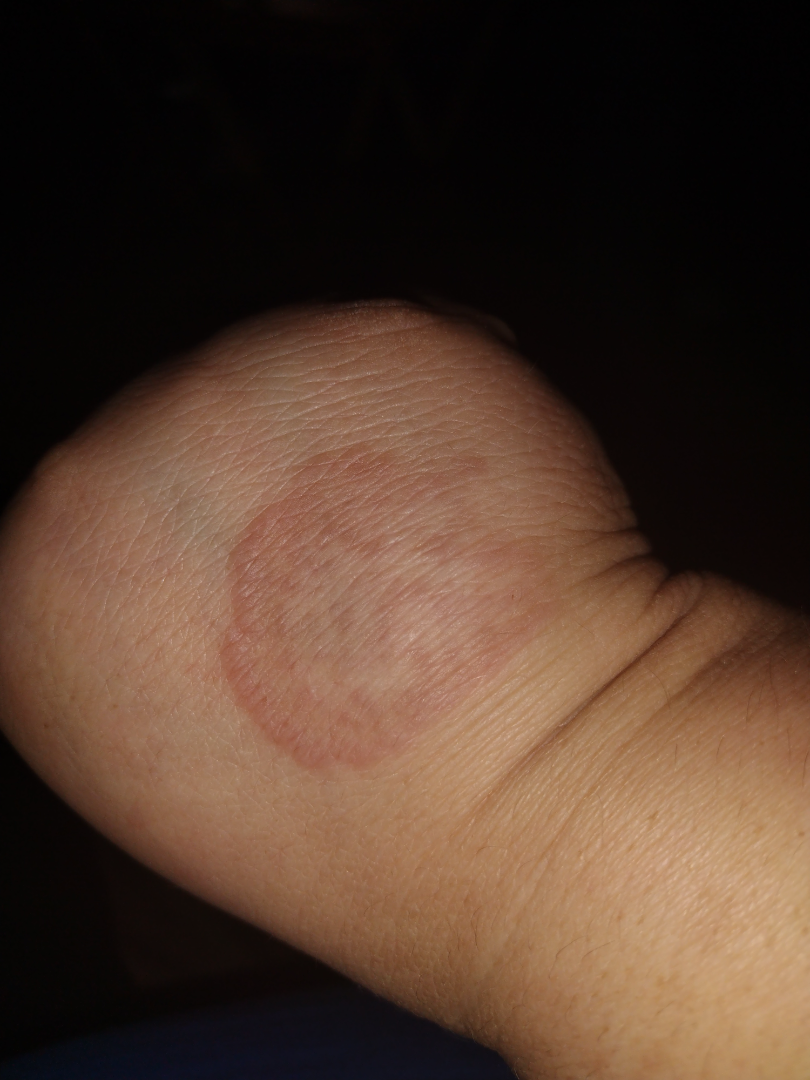* skin tone — human graders estimated Monk skin tone scale 3 or 4
* lesion texture — raised or bumpy
* symptom duration — more than five years
* body site — back of the hand
* view — close-up
* clinical impression — the differential includes Tinea and Granuloma annulare, with no clear leading consideration